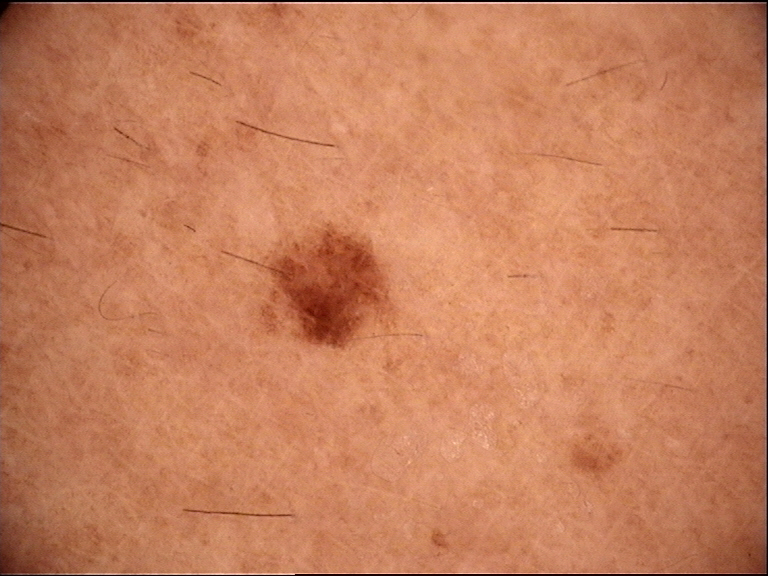A dermatoscopic image of a skin lesion. The diagnosis was a dysplastic junctional nevus.